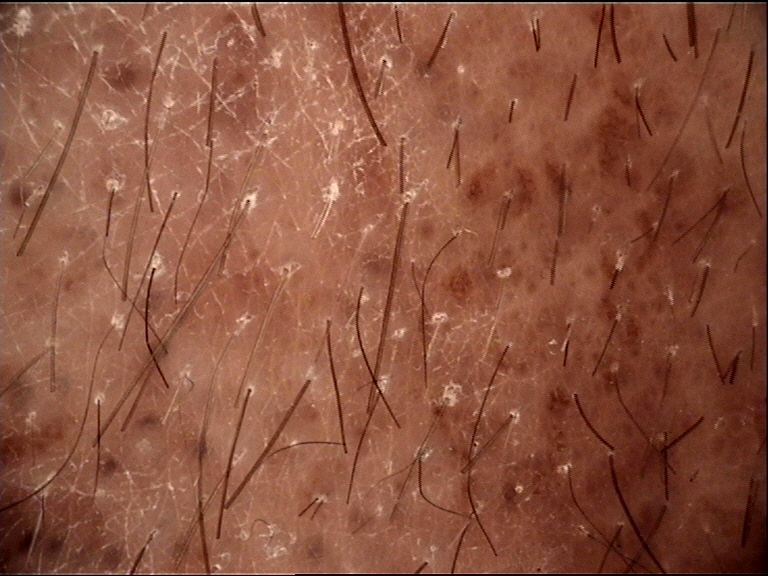image type = dermoscopy
diagnostic label = congenital compound nevus (expert consensus)